A male patient aged 64. The patient says their skin tans without first burning. Dermoscopy of a skin lesion.
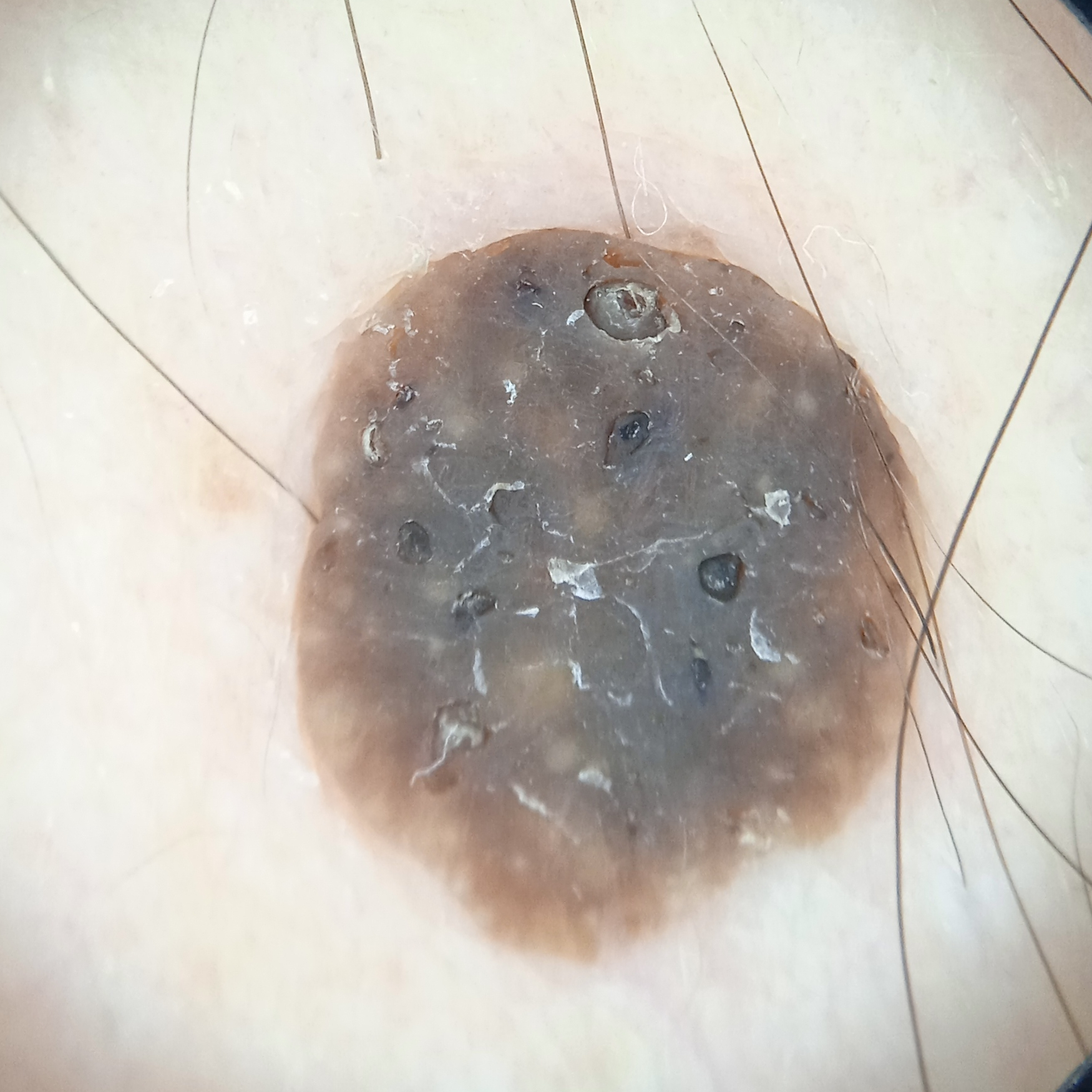The four-dermatologist consensus diagnosis was a seborrheic keratosis; agreement among the reviewers was unanimous; the reviewers were highly confident.